The arm is involved · the patient is a male aged 18–29 · the photograph was taken at a distance: 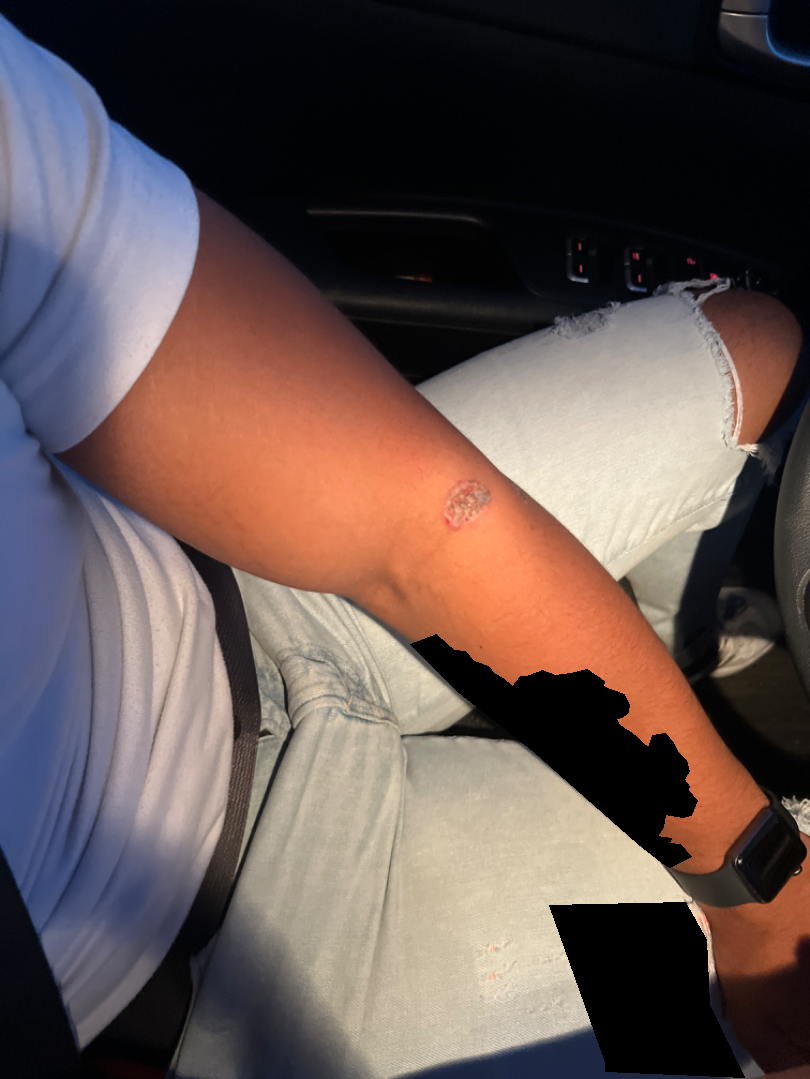Q: What is the dermatologist's impression?
A: the differential is split between Ecthyma, Fungal dermatitis and Cutaneous leishmaniasis